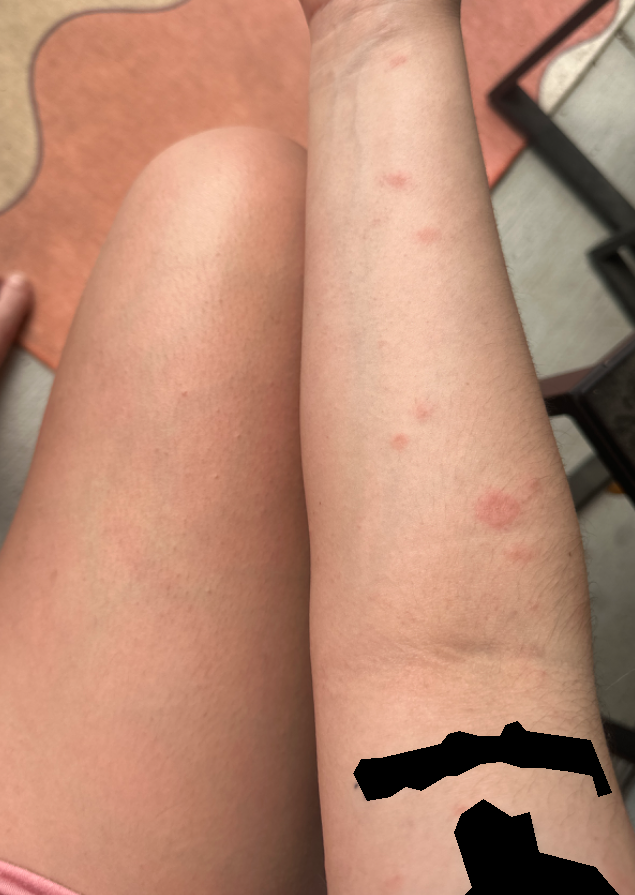Background:
No associated systemic symptoms reported. An image taken at a distance. The lesion is associated with itching and enlargement. Present for one to four weeks. The patient considered this a rash. Located on the back of the hand, leg, arm, head or neck, front of the torso and back of the torso. The lesion is described as rough or flaky and raised or bumpy.
Findings:
Eczema (100%).